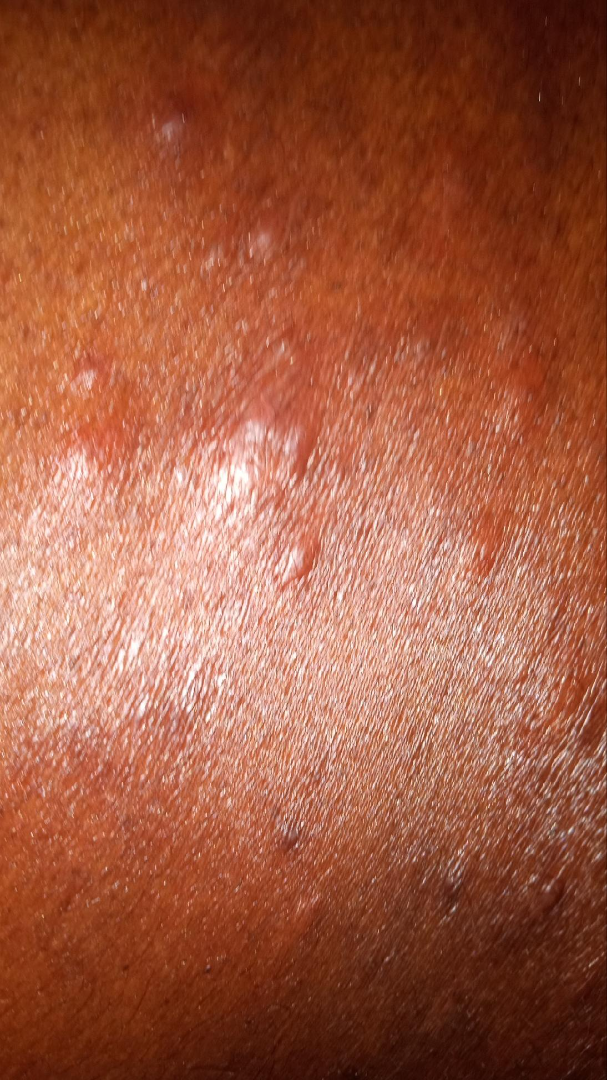Review: The reviewing dermatologist was unable to assign a differential diagnosis from the image. Patient information: The patient is male. Reported duration is more than one year. The patient reports the lesion is raised or bumpy. A close-up photograph. The patient reported no systemic symptoms. FST VI; lay graders estimated a Monk Skin Tone of 7. The lesion involves the back of the torso, arm, head or neck and front of the torso. The patient reports itching, darkening, burning and bothersome appearance. Self-categorized by the patient as a rash.